The patient says their skin reddens with sun exposure. Collected as part of a research study, without a referral diagnosis. A moderate number of moles by the patient's own estimate. A female patient age 27. A dermoscopy image of a skin lesion: 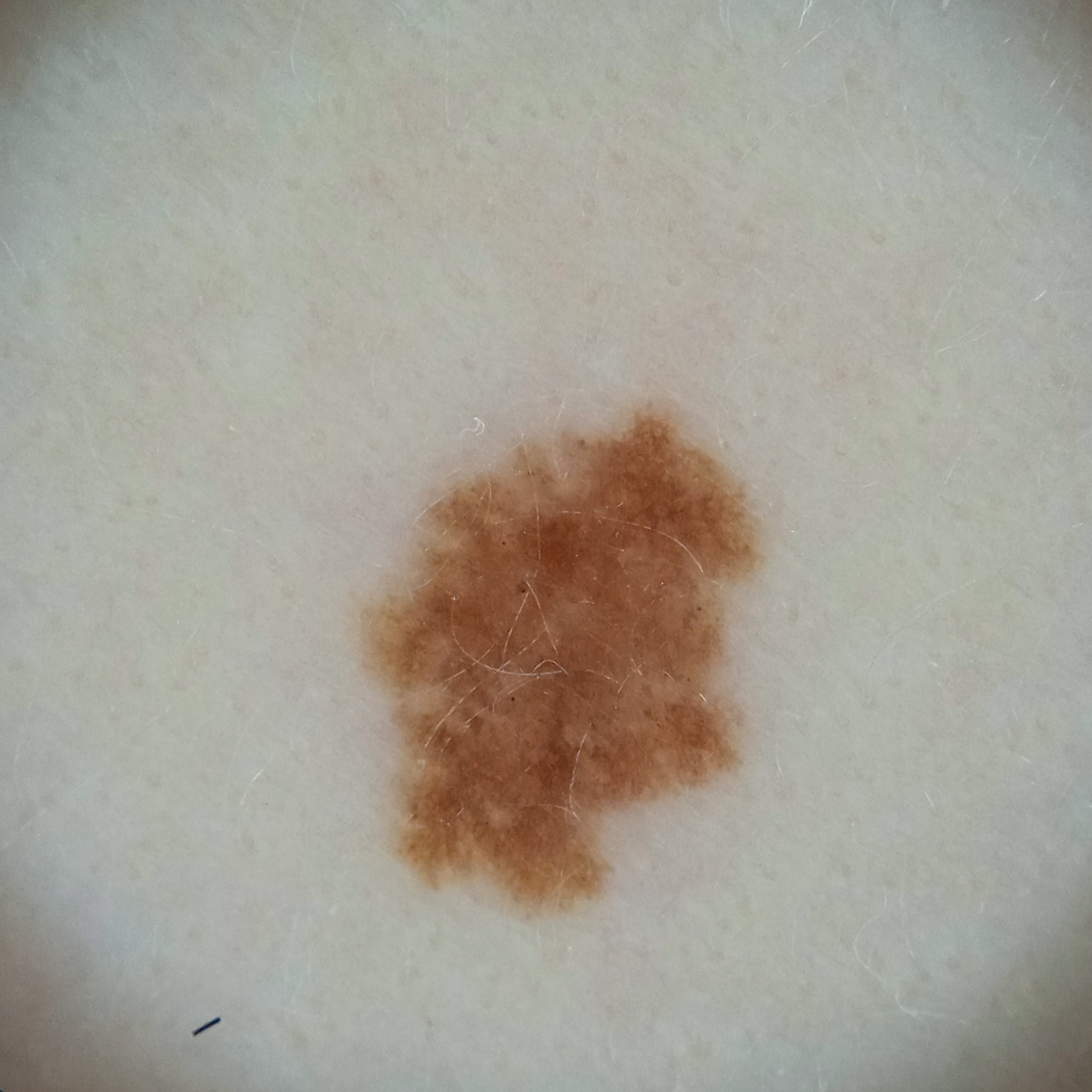<case>
  <lesion_location>an arm</lesion_location>
  <lesion_size>
    <diameter_mm>6.4</diameter_mm>
  </lesion_size>
  <diagnosis>
    <name>atypical (dysplastic) nevus</name>
    <malignancy>benign</malignancy>
  </diagnosis>
</case>